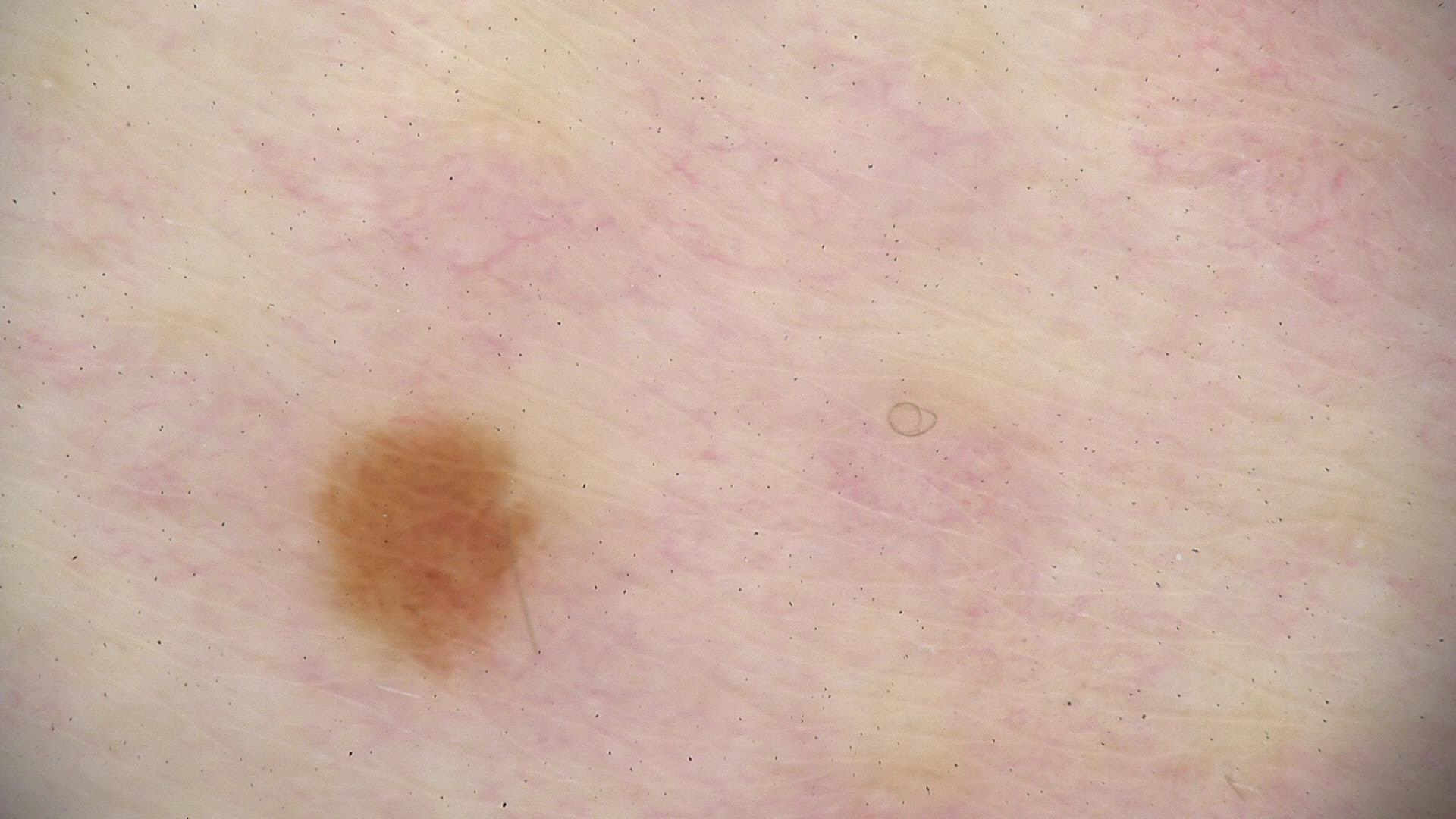image type = dermoscopy, assessment = junctional nevus (expert consensus).